A dermatoscopic image of a skin lesion: 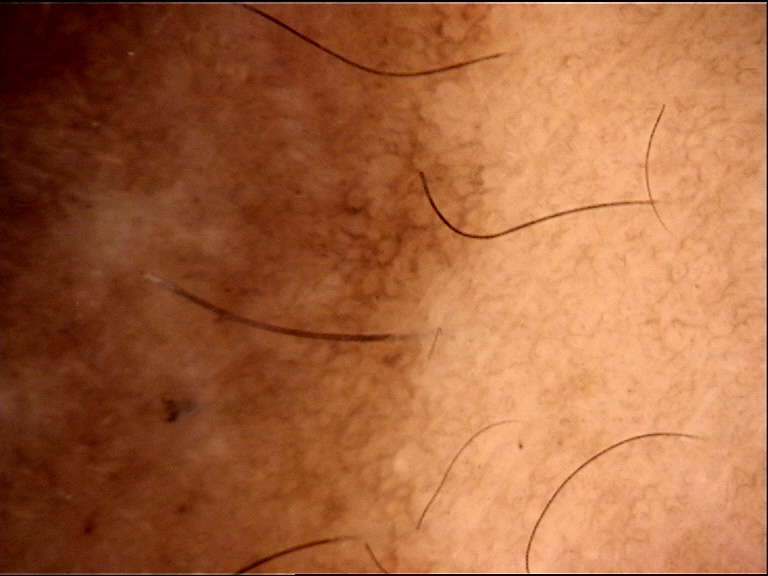Q: What was the diagnostic impression?
A: congenital compound nevus (expert consensus)